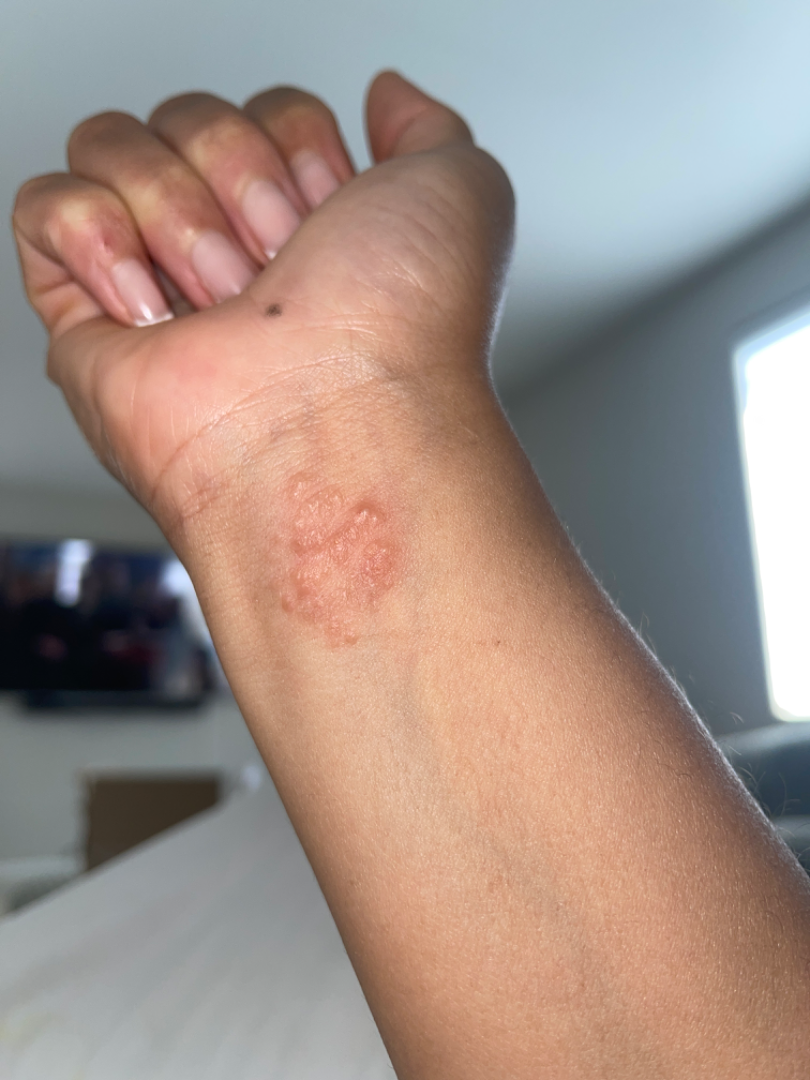Clinical context:
FST IV; lay reviewers estimated Monk skin tone scale 4 or 5 (two reviewer pools). Reported duration is one to four weeks. Texture is reported as rough or flaky and raised or bumpy. Female patient, age 30–39. The patient described the issue as a rash. This is a close-up image.
Assessment:
Single-reviewer assessment: the leading consideration is Allergic Contact Dermatitis; possibly Impetigo; an alternative is Herpes Zoster.